The patient described the issue as a rash, the contributor notes the condition has been present for less than one week, the photograph is a close-up of the affected area, reported lesion symptoms include itching, the patient reported no systemic symptoms, FST IV; lay graders estimated Monk Skin Tone 3 or 5 (two reviewer pools disagreed), the contributor is a male aged 40–49, the lesion involves the arm — 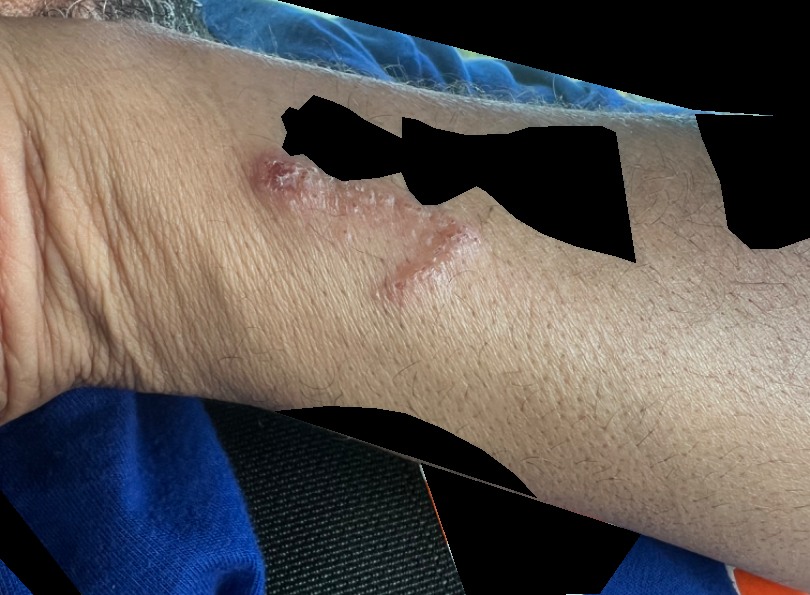| feature | finding |
|---|---|
| assessment | indeterminate |